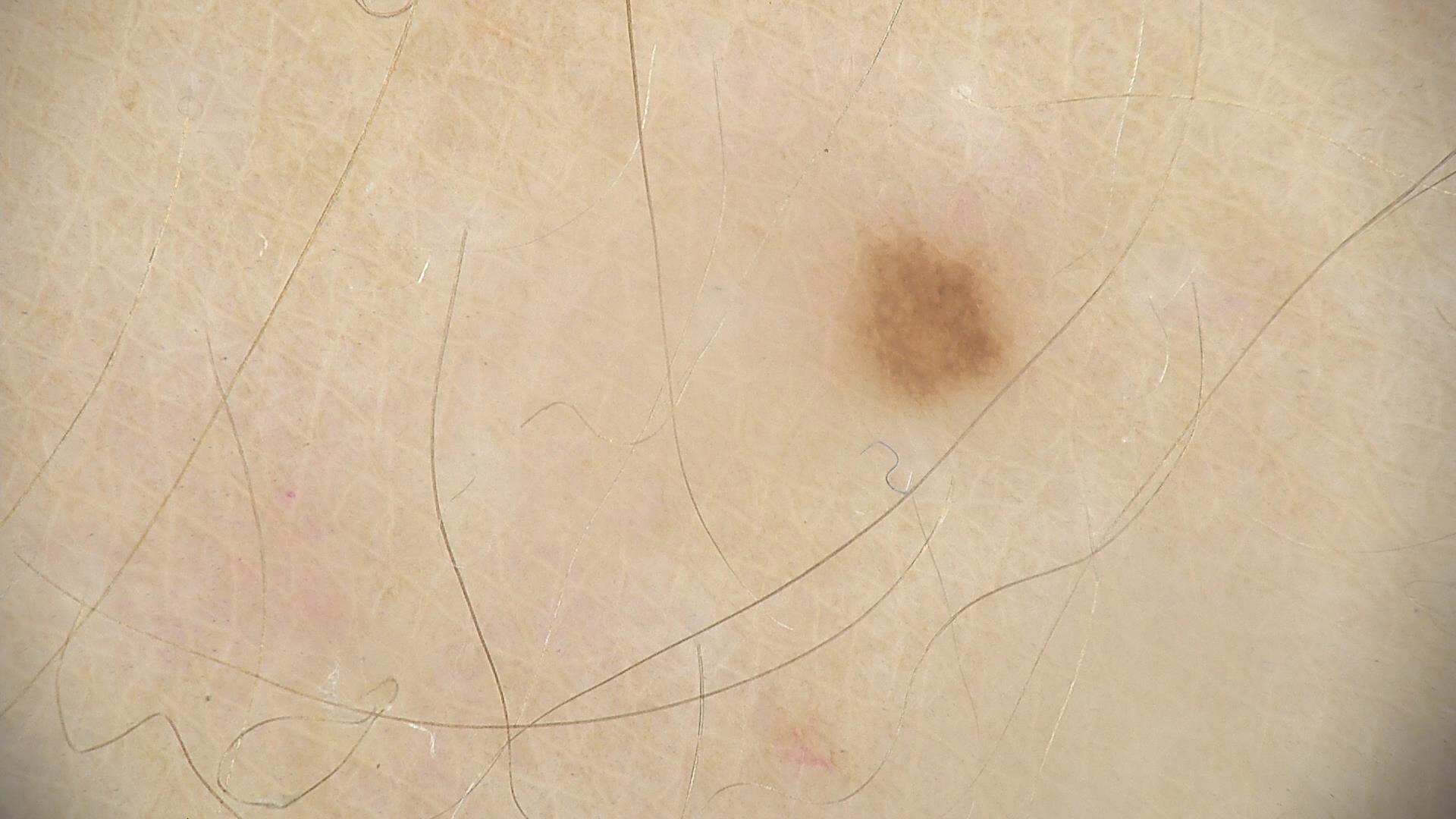image type — dermatoscopy; assessment — dysplastic junctional nevus (expert consensus).